No associated systemic symptoms reported; the lesion is associated with burning, bothersome appearance, darkening, itching and enlargement; the lesion involves the arm; this is a close-up image; the contributor is a male aged 40–49; the patient notes the condition has been present for one to three months — 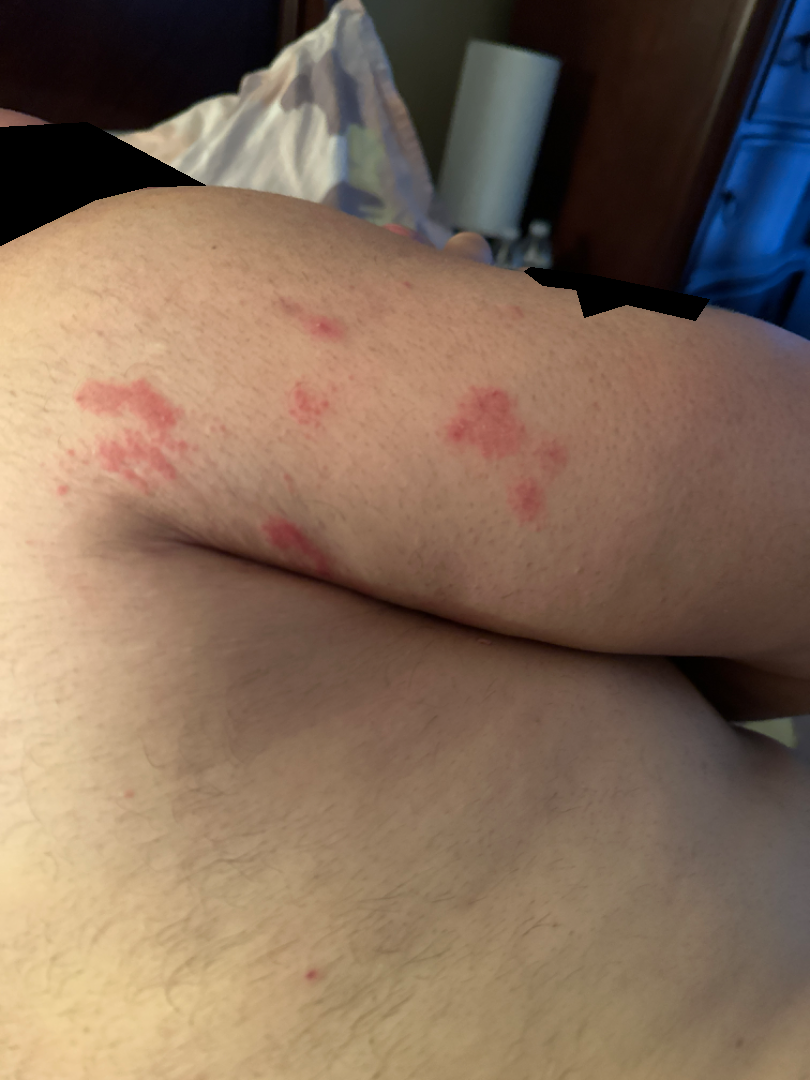Notes:
* impression — the leading consideration is Eczema; the differential also includes Psoriasis